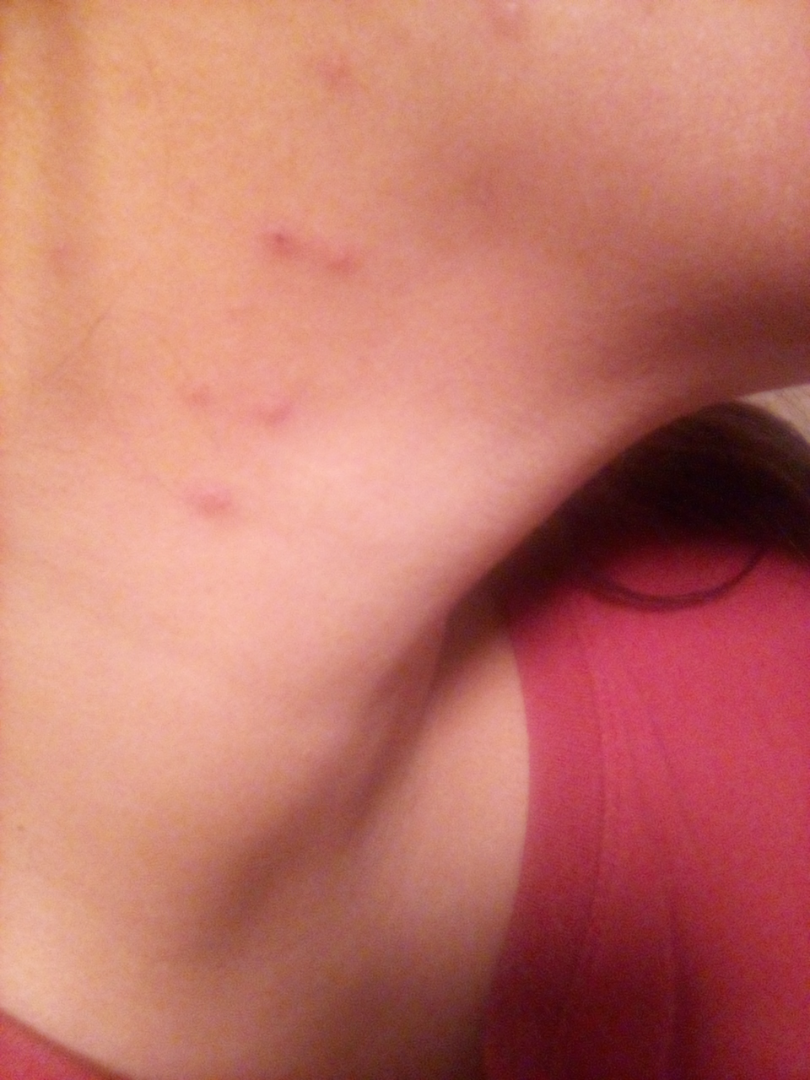The affected area is the head or neck. Texture is reported as raised or bumpy. The lesion is associated with itching and bothersome appearance. This is a close-up image. Skin tone: Fitzpatrick III; human graders estimated Monk skin tone scale 2–3. The patient reported no systemic symptoms. Insect Bite (leading); Acneiform eruption (considered); Viral Exanthem (lower probability).